A dermoscopic photograph of a skin lesion: 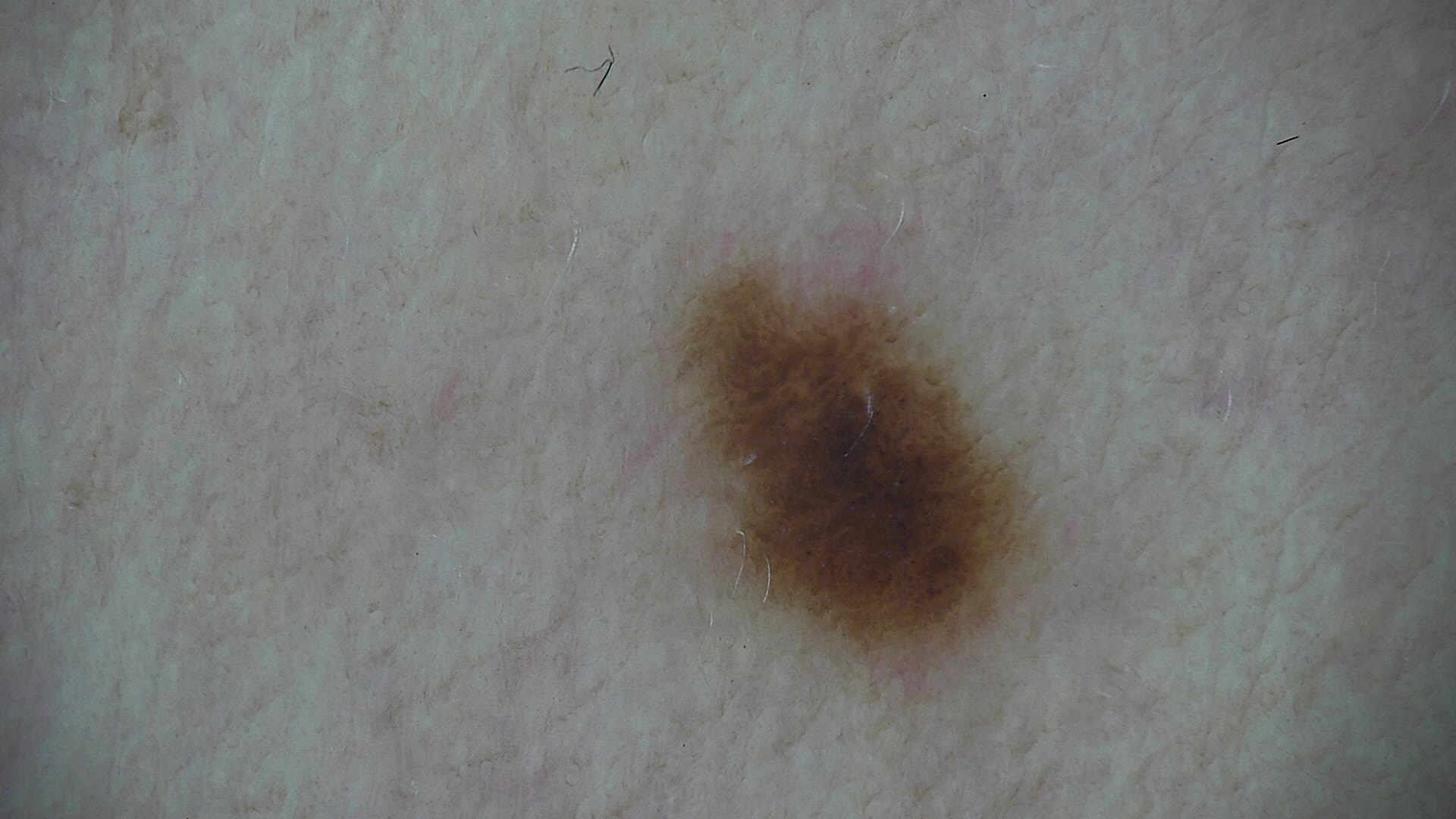Impression: Diagnosed as a dysplastic junctional nevus.